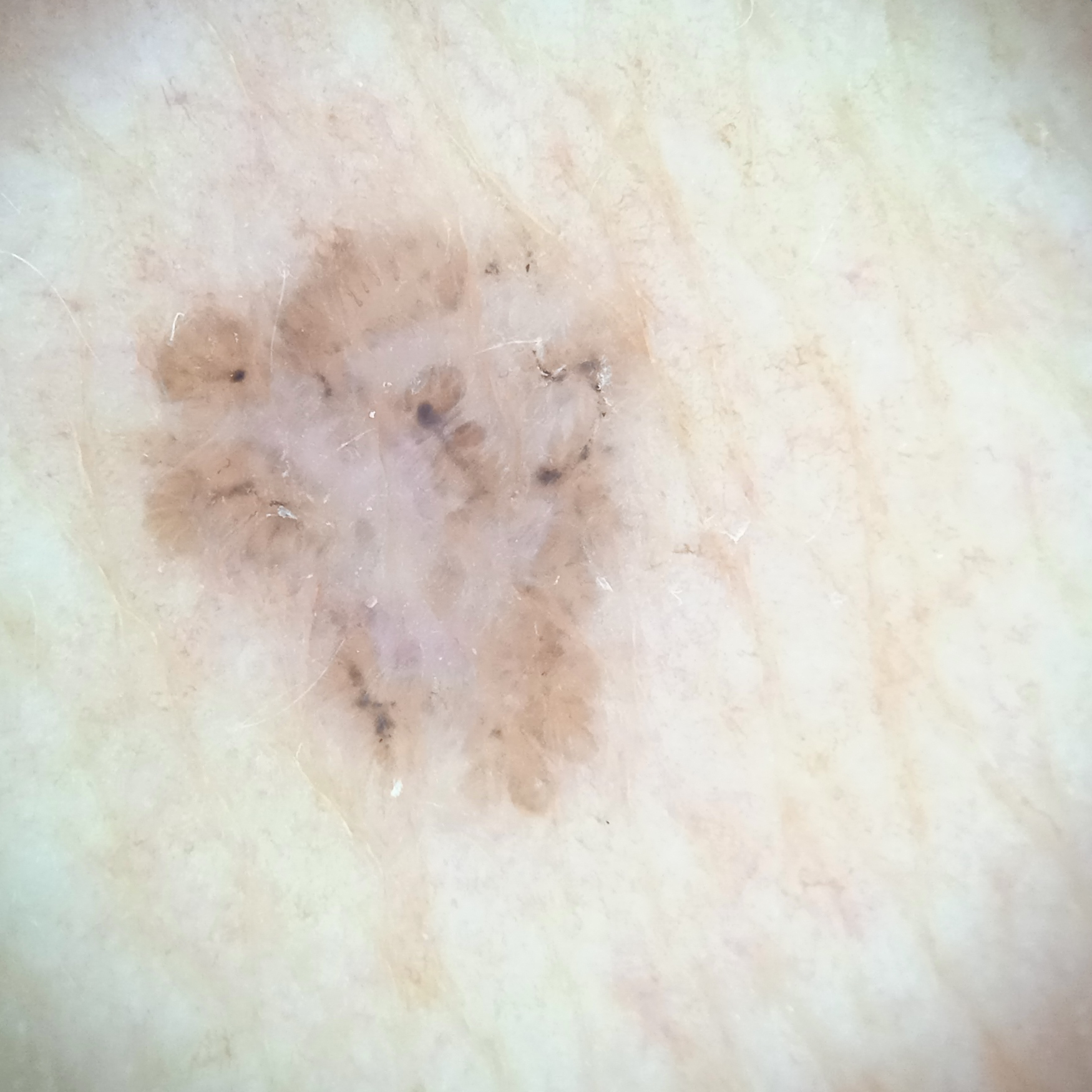Findings: A dermatoscopic image of a skin lesion. The patient says their skin tans without first burning. Few moles overall by the patient's own estimate. A female subject age 60. The patient reports a personal history of skin cancer and a personal history of cancer. The lesion is located on the torso. The lesion is about 7.2 mm across. Impression: The consensus diagnosis for this lesion was a basal cell carcinoma.